An image taken at an angle · located on the top or side of the foot — 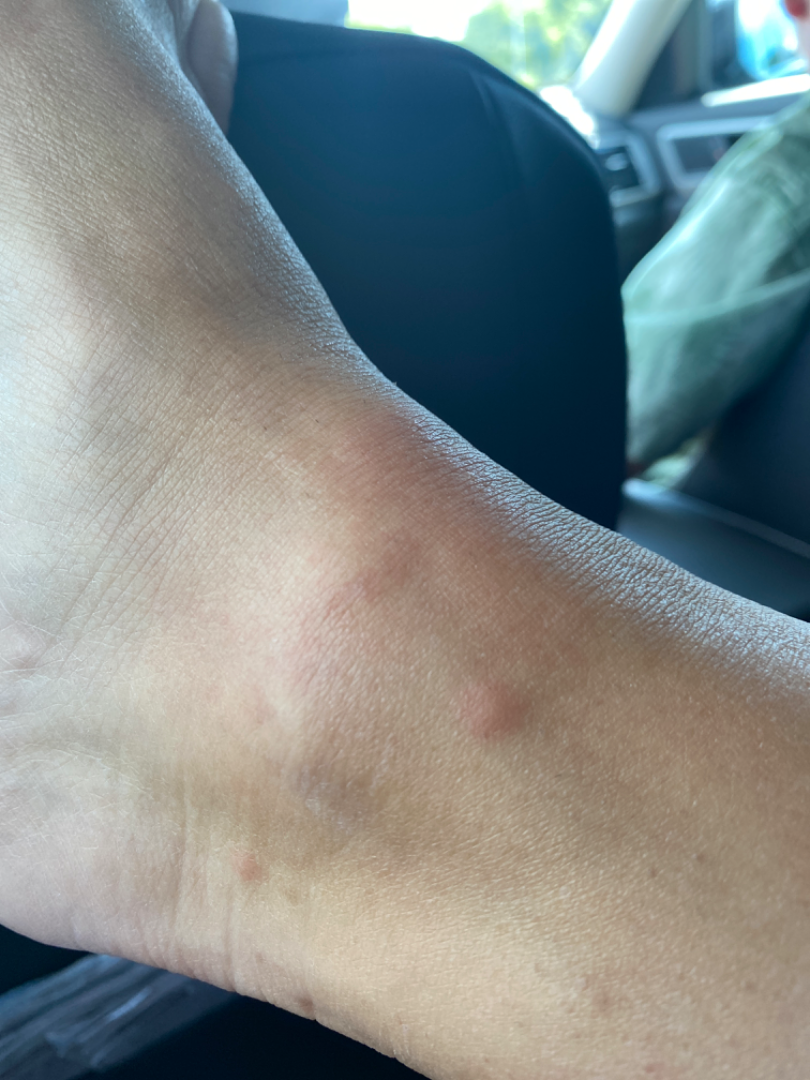assessment=none discernible; history=about one day; patient describes the issue as=a rash; lesion symptoms=bothersome appearance and itching; surface texture=raised or bumpy and fluid-filled.